No associated systemic symptoms reported. Reported duration is one to four weeks. Male contributor, age 40–49. Texture is reported as raised or bumpy. The arm is involved. Symptoms reported: bothersome appearance and itching. The photo was captured at a distance: 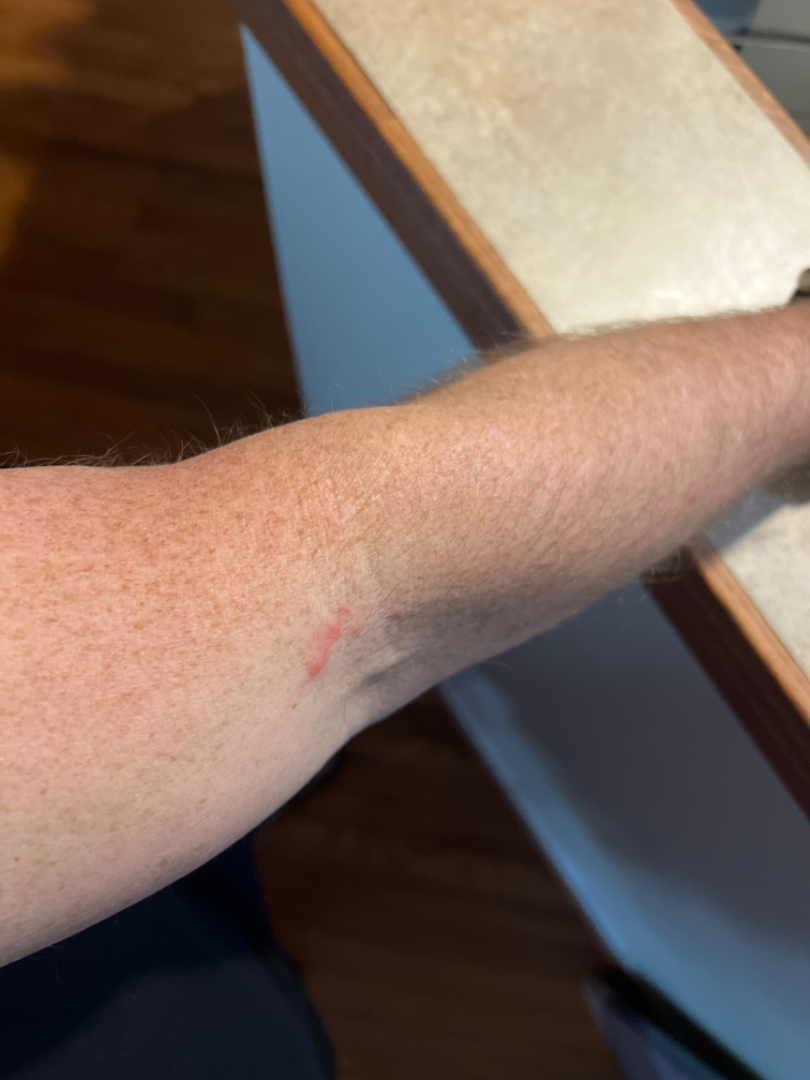Q: What conditions are considered?
A: most likely Contact dermatitis